The photograph is a close-up of the affected area.
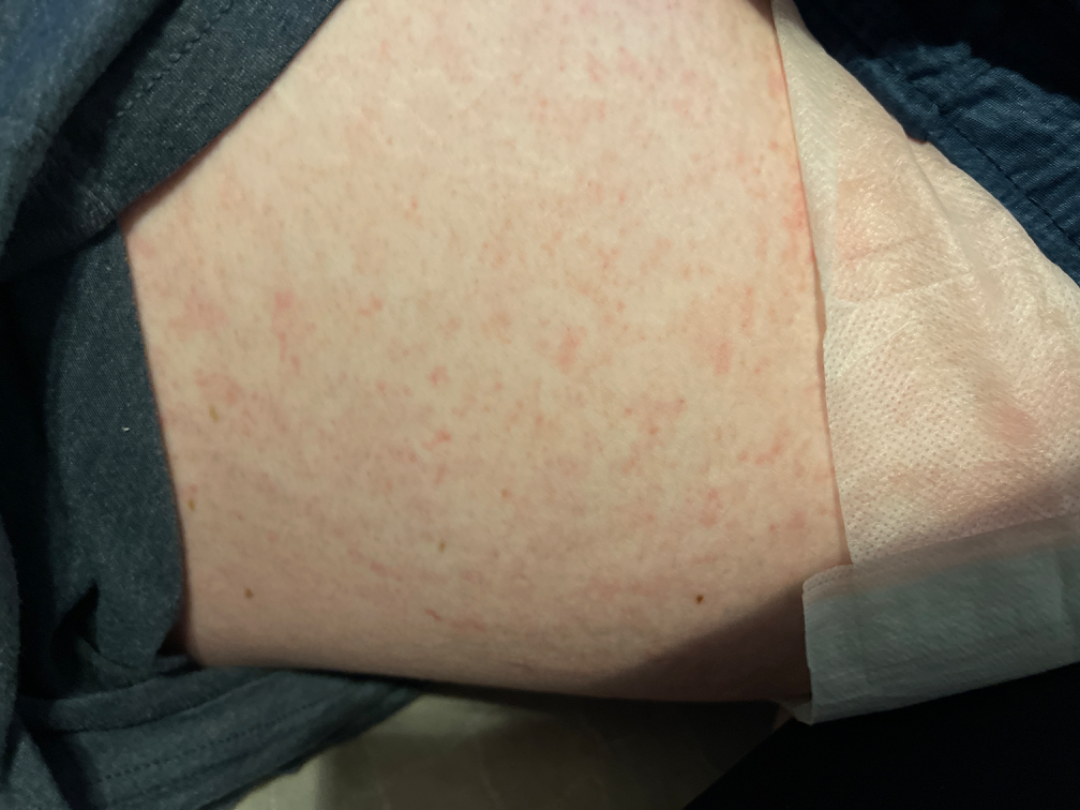Assessment: The reviewing dermatologist's impression was: Drug Rash, Viral Exanthem and Hypersensitivity were considered with similar weight.